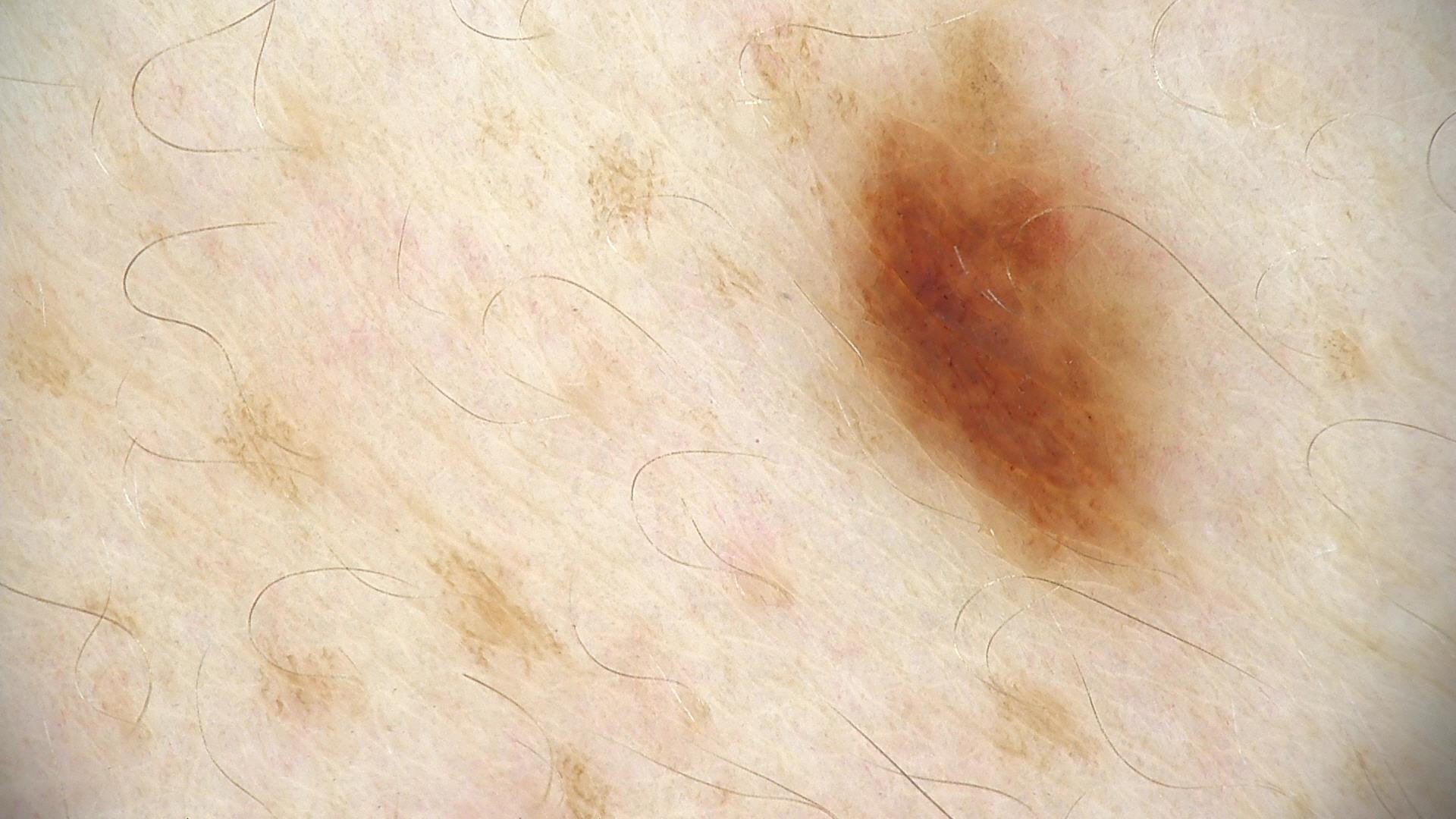Conclusion: The diagnostic label was a dysplastic junctional nevus.